The patient says their skin reddens with sun exposure; dermoscopy of a skin lesion; few moles overall by the patient's own estimate; collected as part of a research study, without a referral diagnosis; on a questionnaire the patient reported a personal history of cancer — 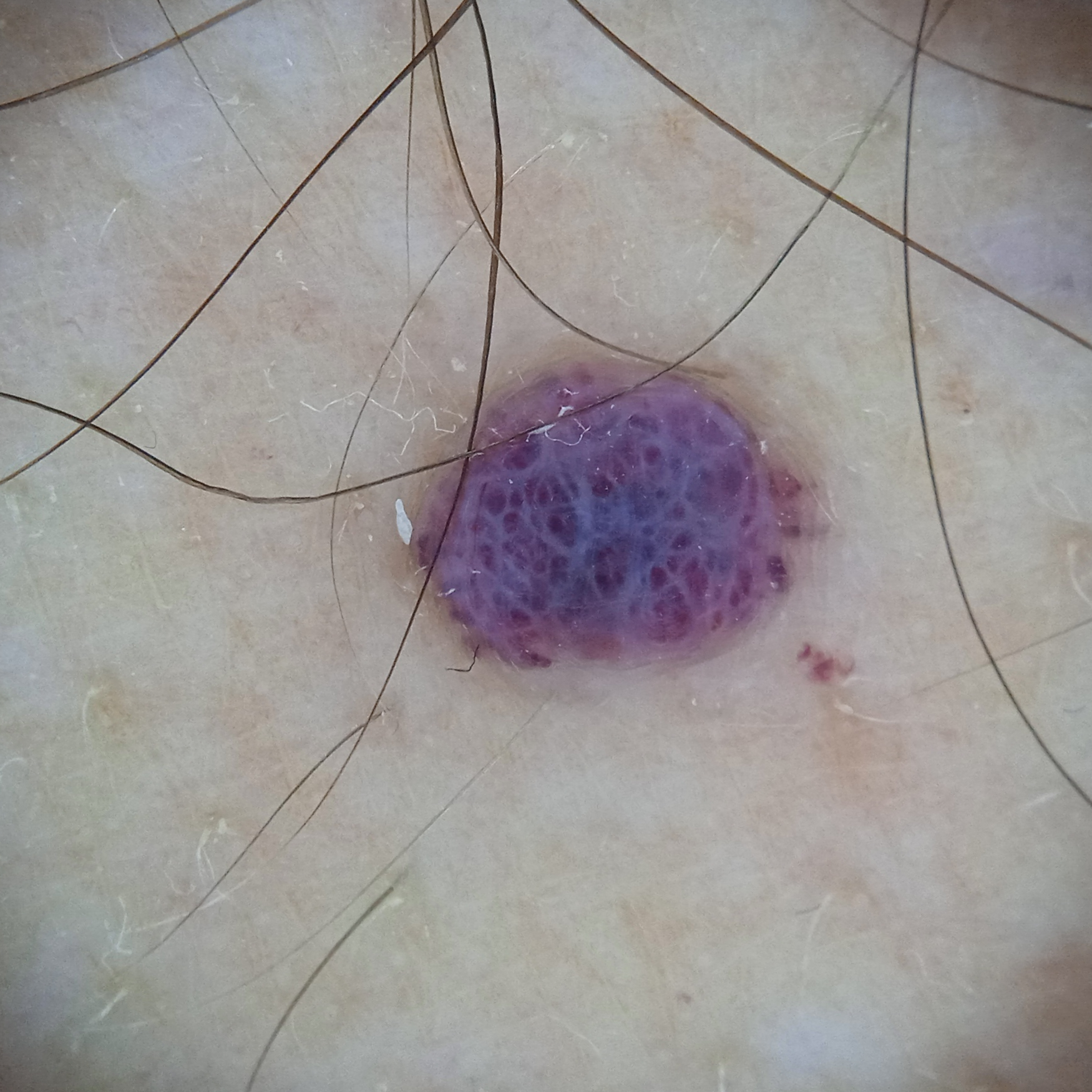site: the torso
lesion size: 4.7 mm
diagnostic label: angioma (dermatologist consensus)